A dermatoscopic image of a skin lesion · the patient describes having a moderate number of moles · imaged for a research study, with no referral diagnosis recorded · the patient reports no immunosuppression and no personal history of skin cancer · a female patient age 50 · the patient says their skin reddens painfully with sun exposure — 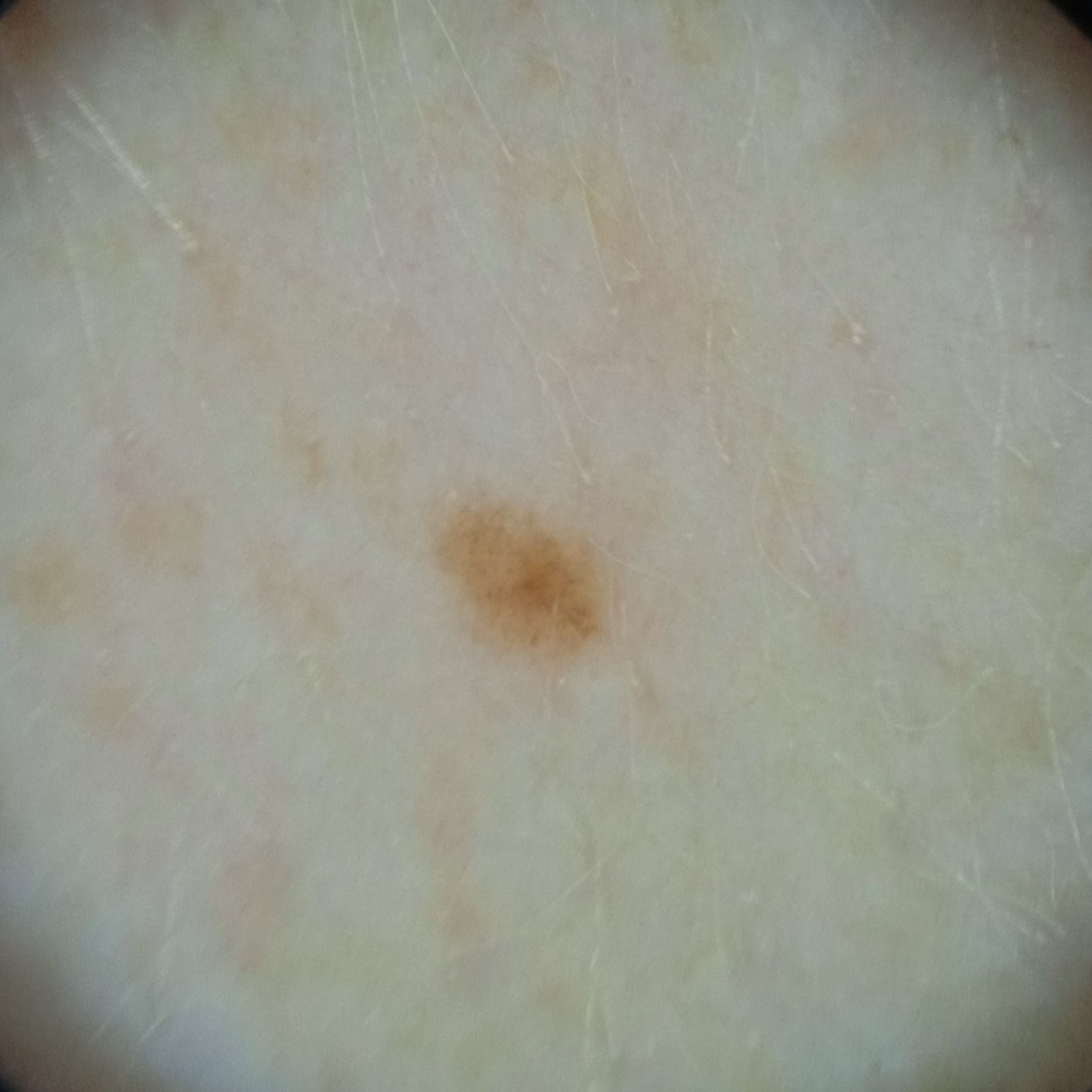Q: What is the anatomic site?
A: an arm
Q: How large is the lesion?
A: 2 mm
Q: What was the diagnosis?
A: melanocytic nevus (dermatologist consensus)